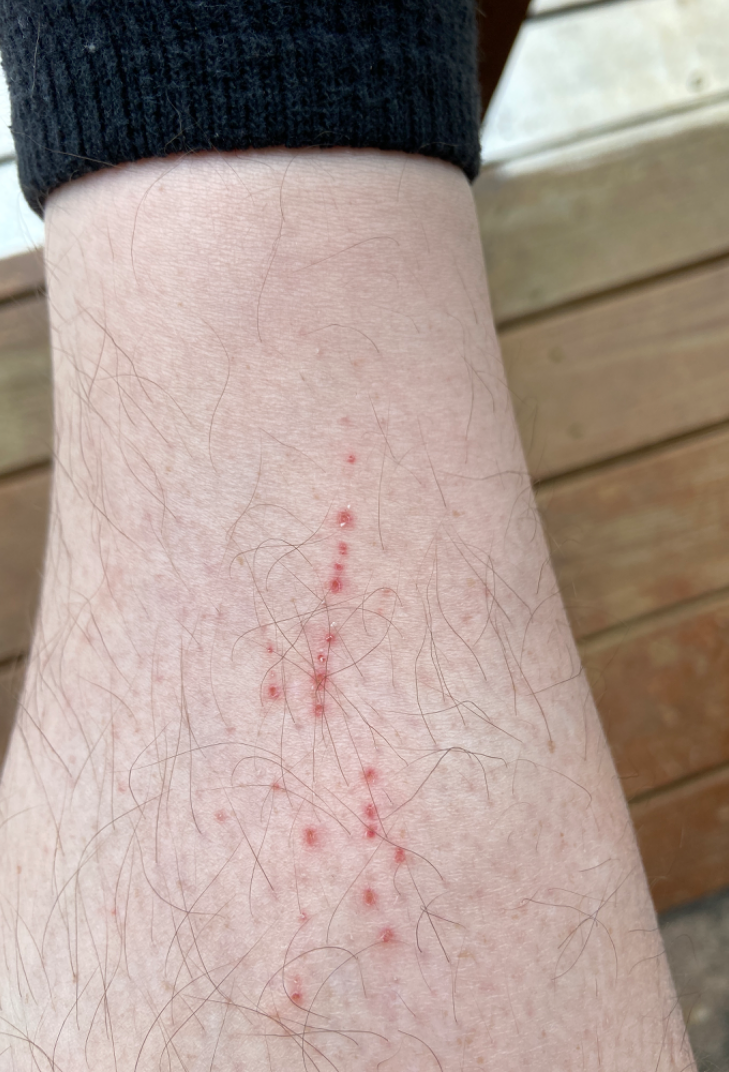The case was difficult to assess from the available photograph.
The subject is a male aged 18–29.
The lesion involves the leg.
Reported duration is about one day.
Texture is reported as flat.
The patient described the issue as a rash.
The contributor reports itching.
This is a close-up image.